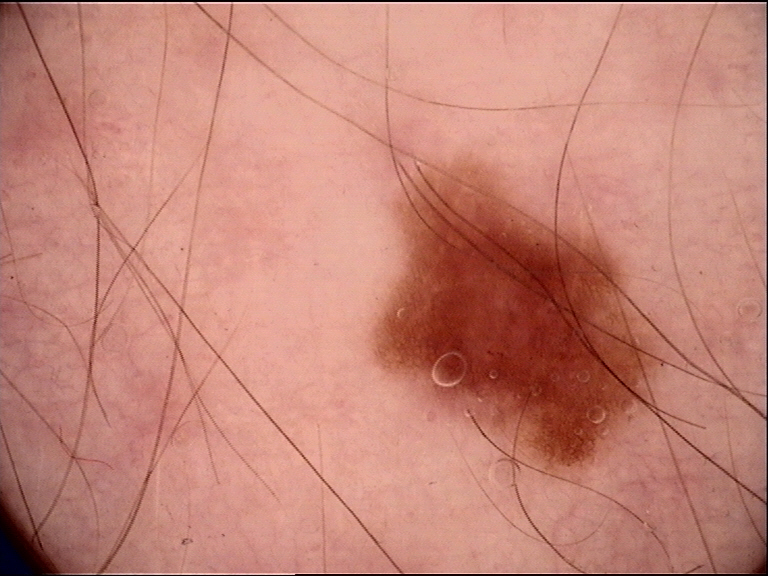A dermoscopic image of a skin lesion.
Classified as a dysplastic junctional nevus.